A clinical overview photograph of a skin lesion · a male subject in their 60s:
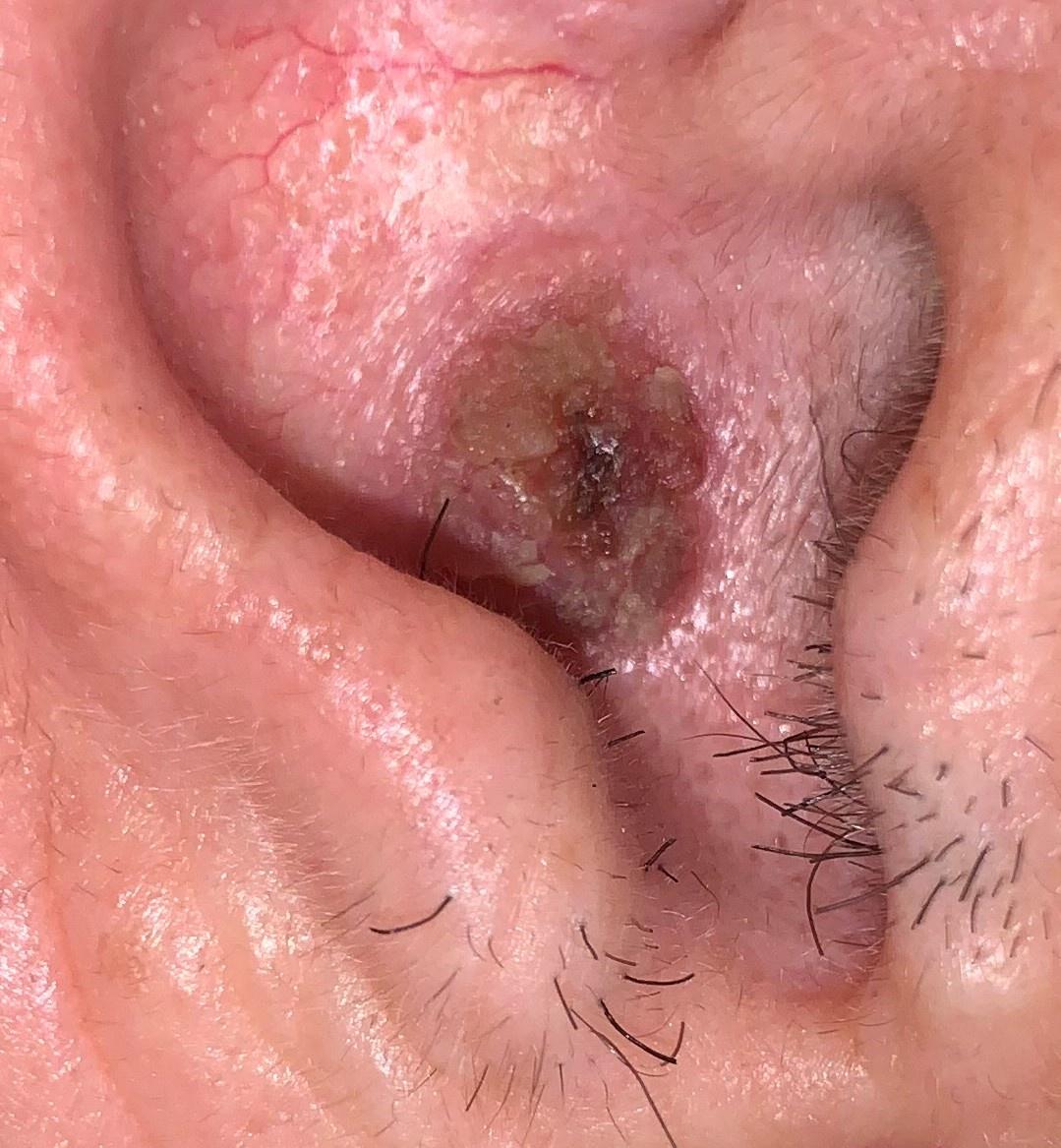The lesion is located on the head or neck.
On biopsy, the diagnosis was a lesion of epidermal origin — a squamous cell carcinoma.